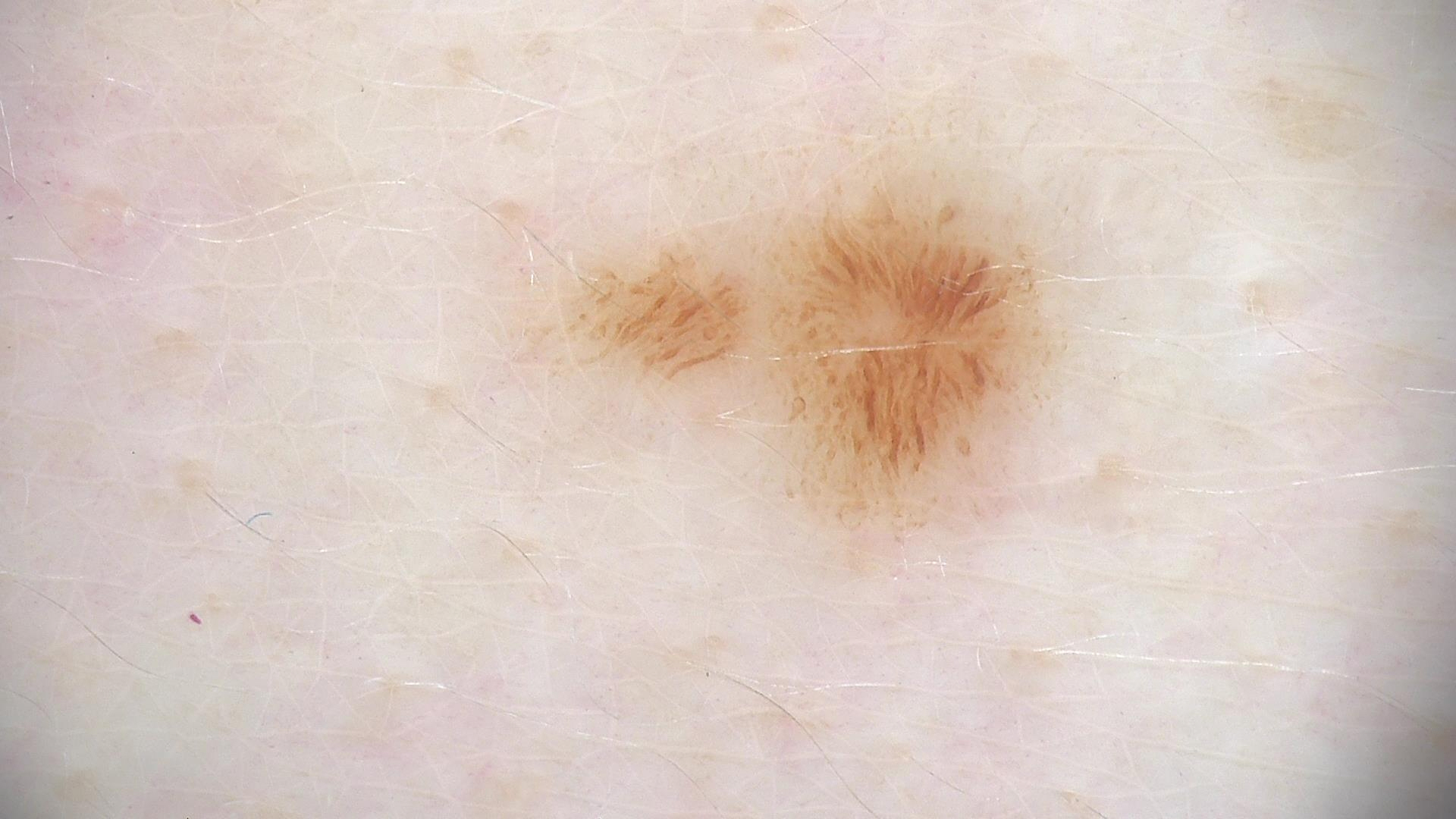Case: A skin lesion imaged with a dermatoscope. Conclusion: Diagnosed as a dysplastic junctional nevus.